The patient is a male roughly 70 years of age, a dermoscopy image of a single skin lesion: 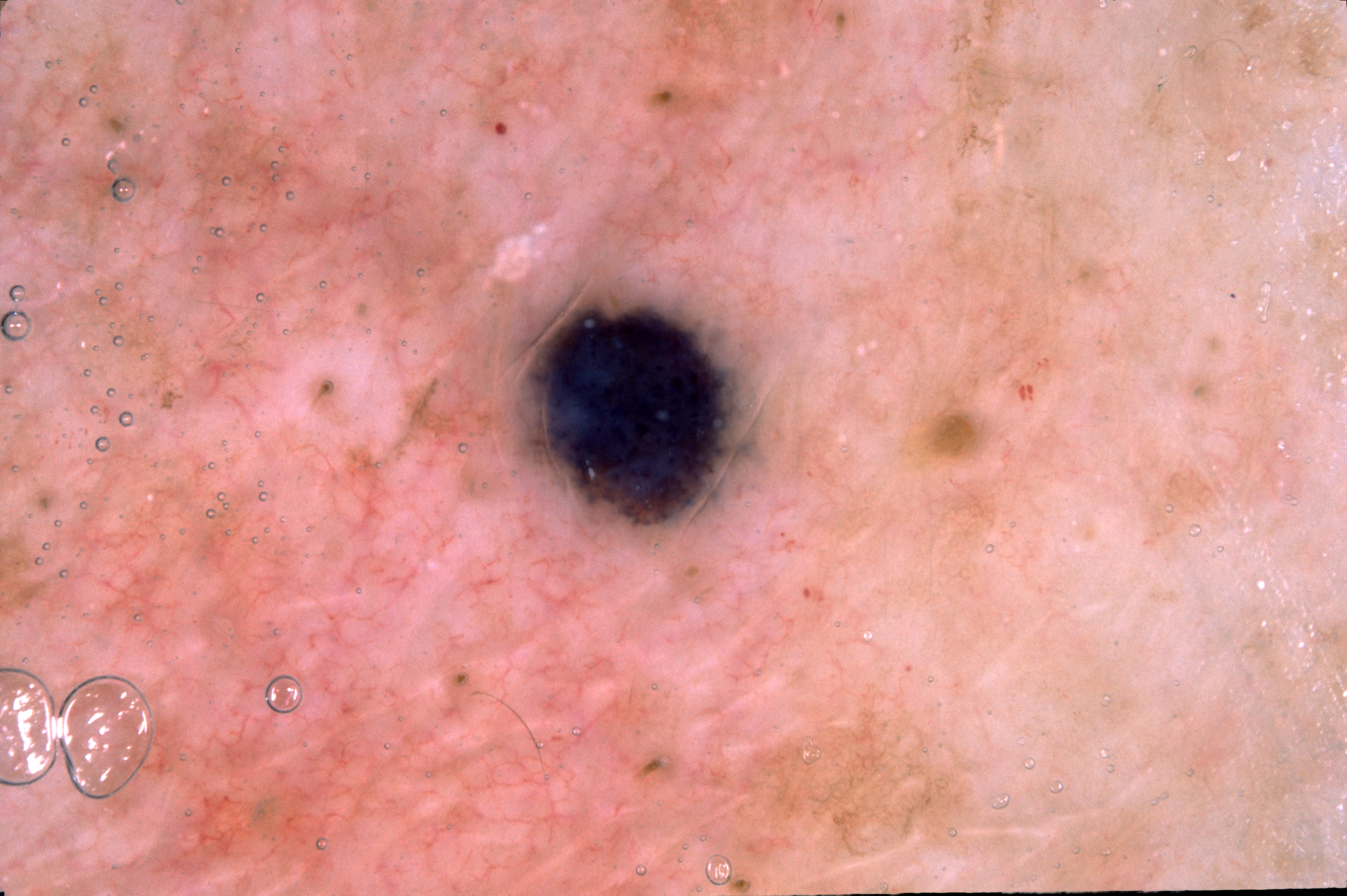absent dermoscopic findings = streaks, pigment network, milia-like cysts, and negative network
bounding box = (507, 271, 763, 534)
size = ~4% of the field
diagnostic label = a melanocytic nevus